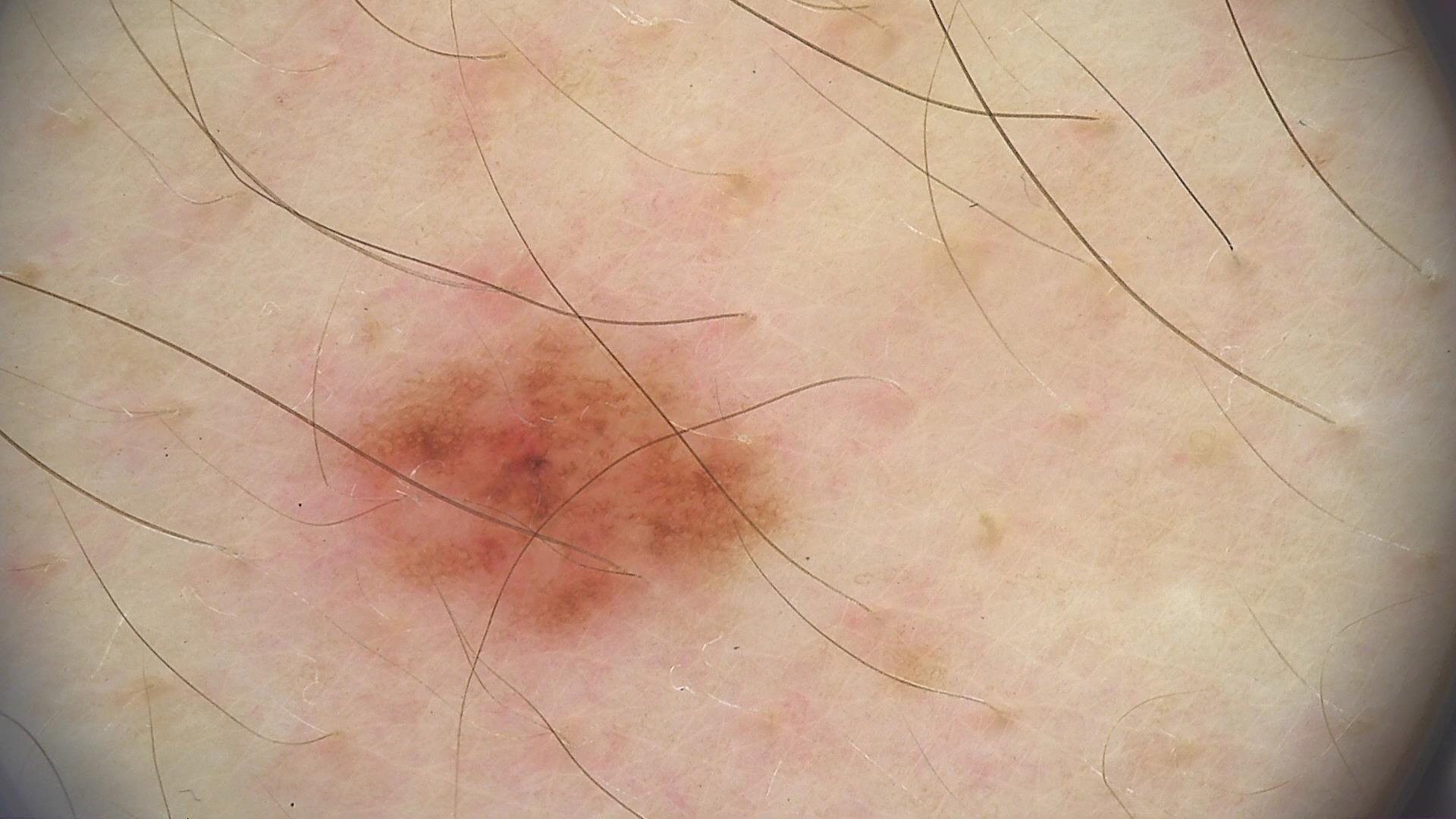Dermoscopy of a skin lesion.
Classified as a dysplastic junctional nevus.